A close-up photograph:
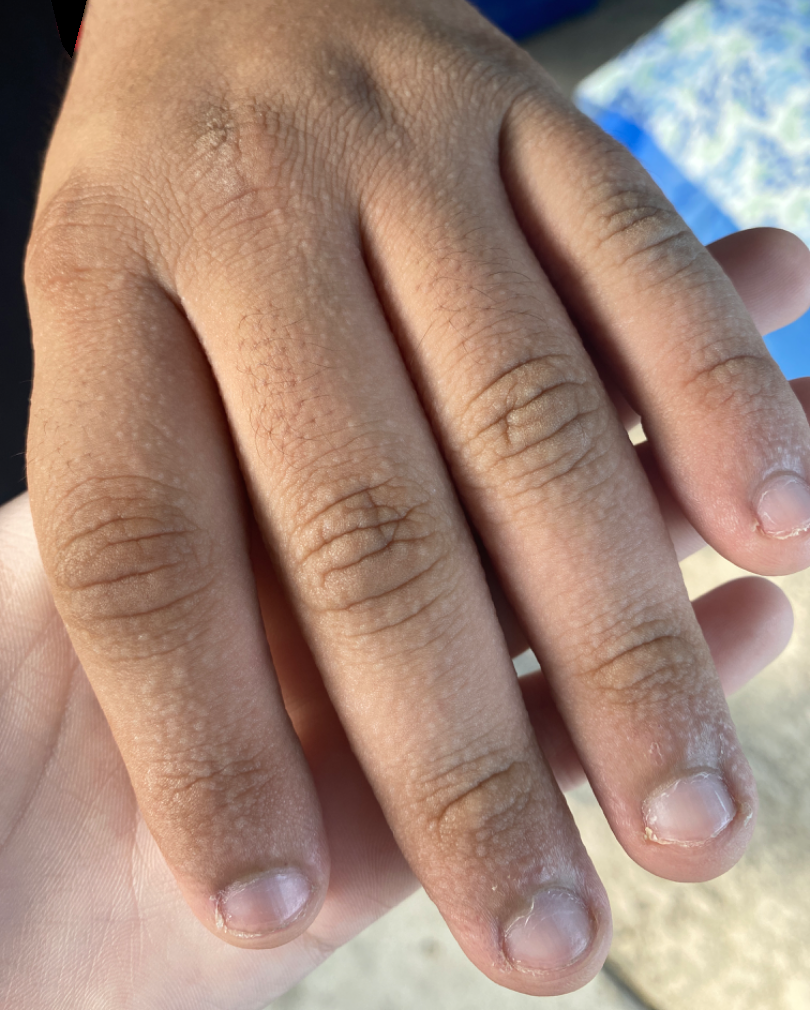Notes:
* skin tone — Fitzpatrick phototype III; human graders estimated MST 4 or 6 (two reviewer pools disagreed)
* dermatologist impression — most consistent with Acrokeratosis verruciformis